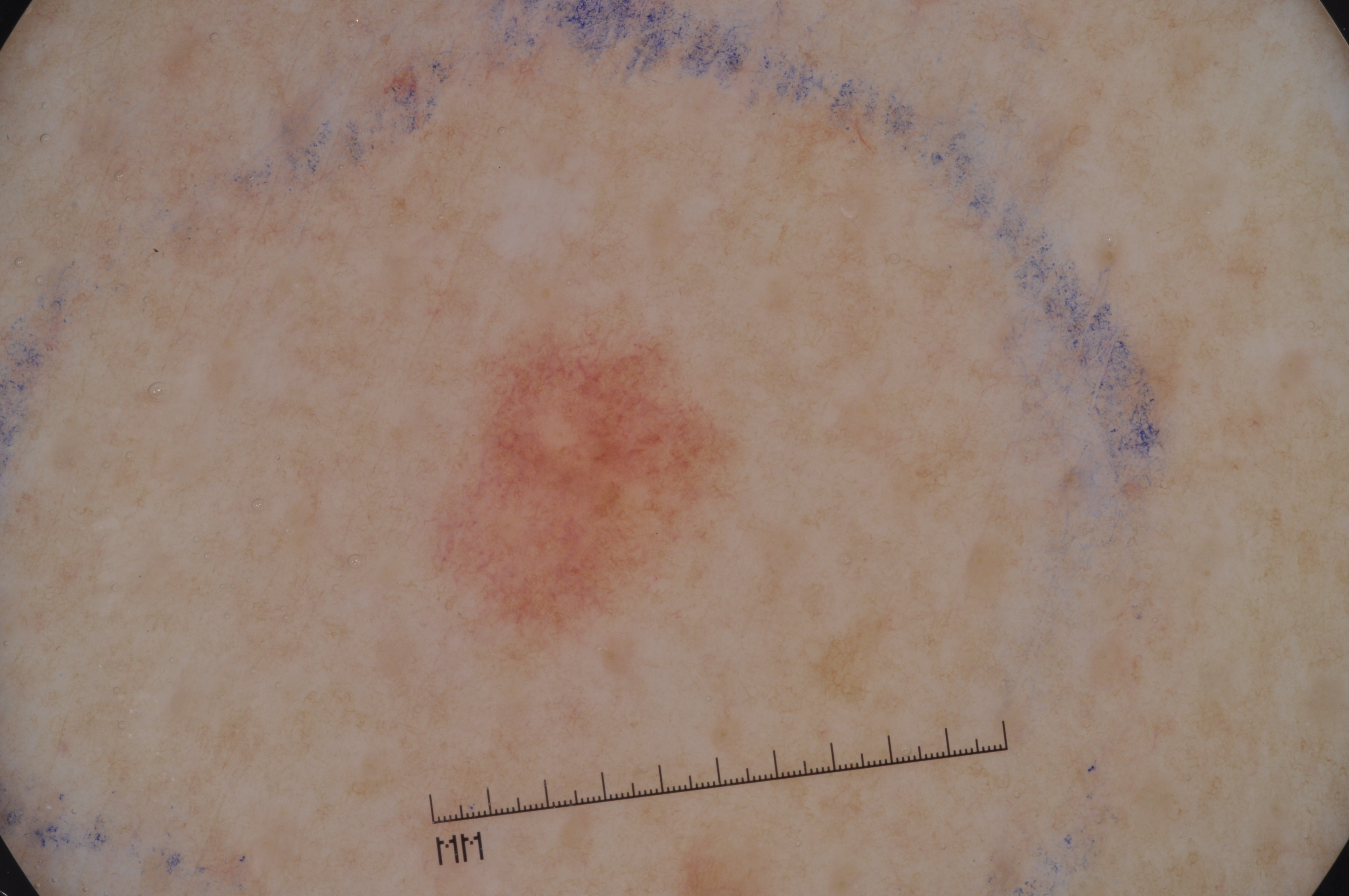patient — female, aged approximately 65
modality — dermoscopy of a skin lesion
lesion bbox — x1=430, y1=293, x2=743, y2=676
absent dermoscopic features — streaks, pigment network, milia-like cysts, and negative network
size — ~6% of the field
assessment — a melanocytic nevus, a benign lesion